A close-up photograph; the patient is 40–49, female; located on the arm: 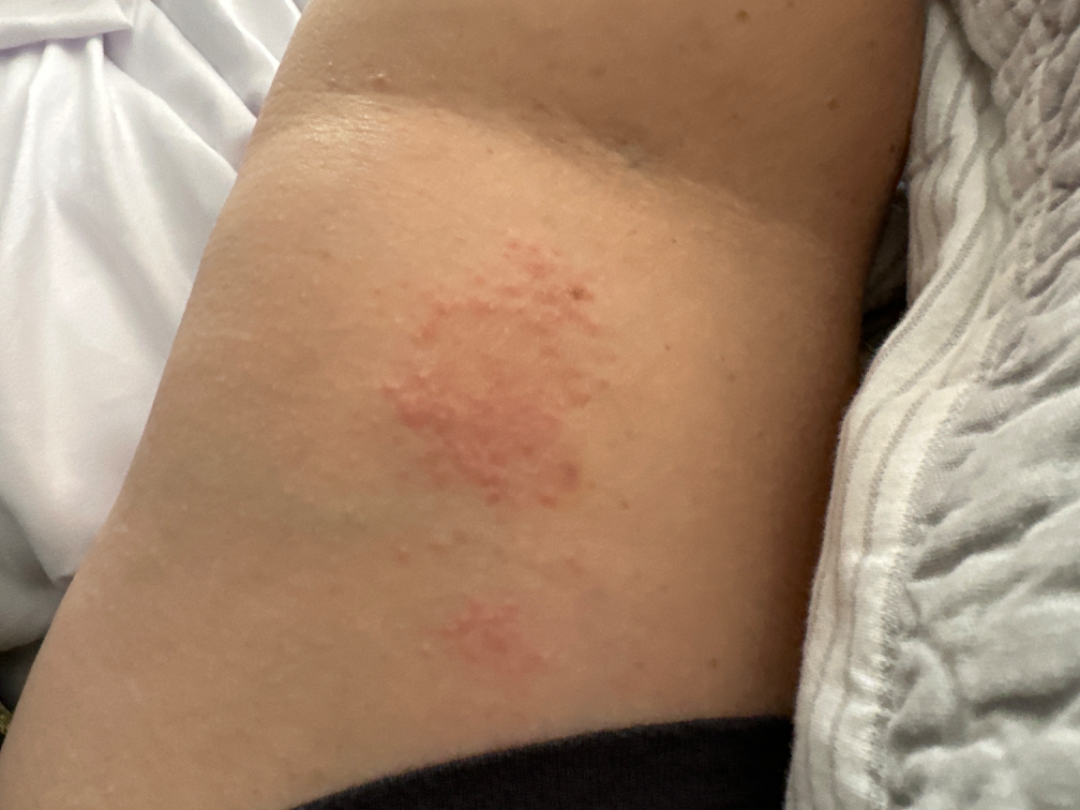symptoms = itching
lesion texture = raised or bumpy
assessment = Eczema (considered); Allergic Contact Dermatitis (considered)